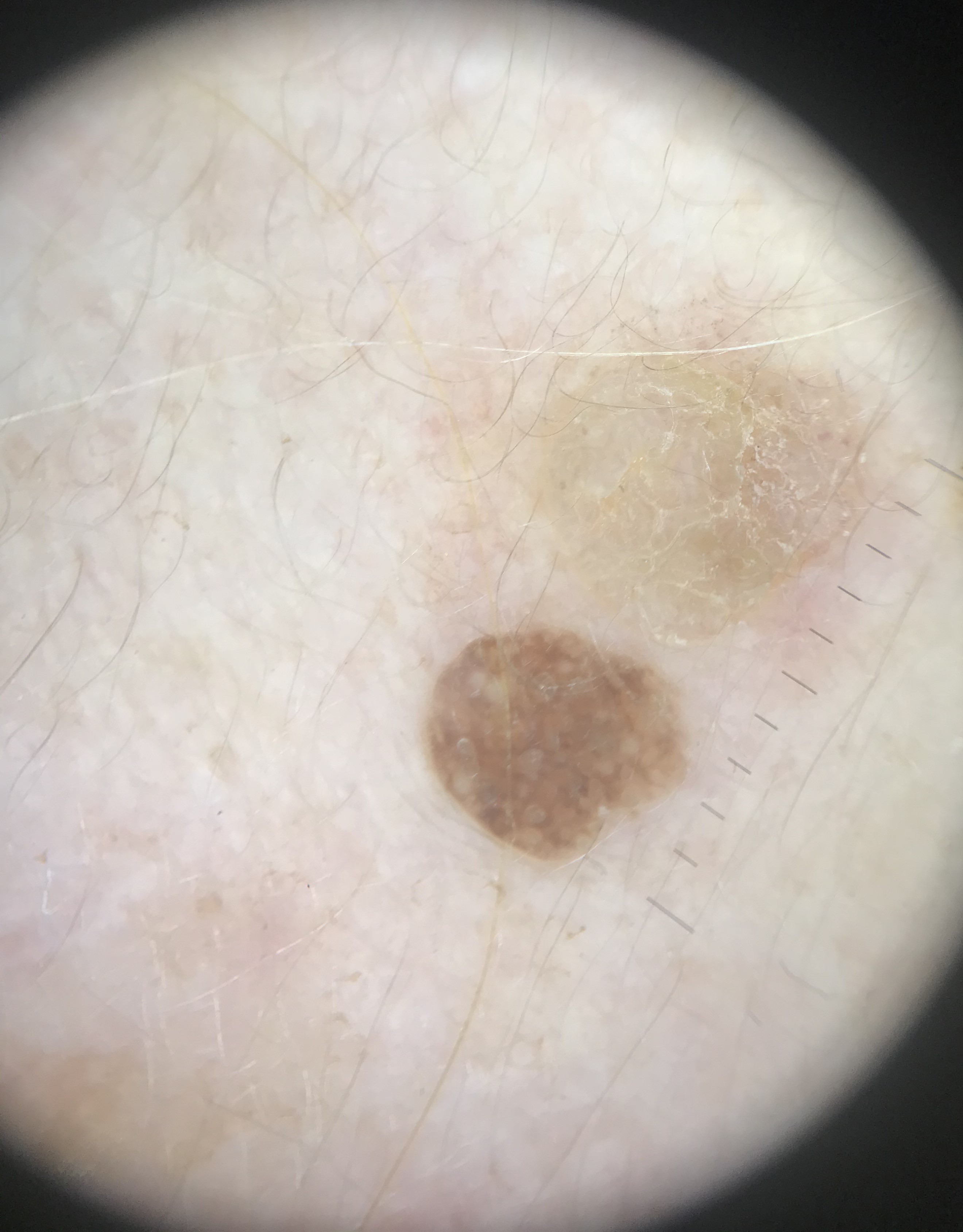{
  "diagnosis": {
    "name": "seborrheic keratosis",
    "code": "sk",
    "malignancy": "benign",
    "super_class": "non-melanocytic",
    "confirmation": "expert consensus"
  }
}